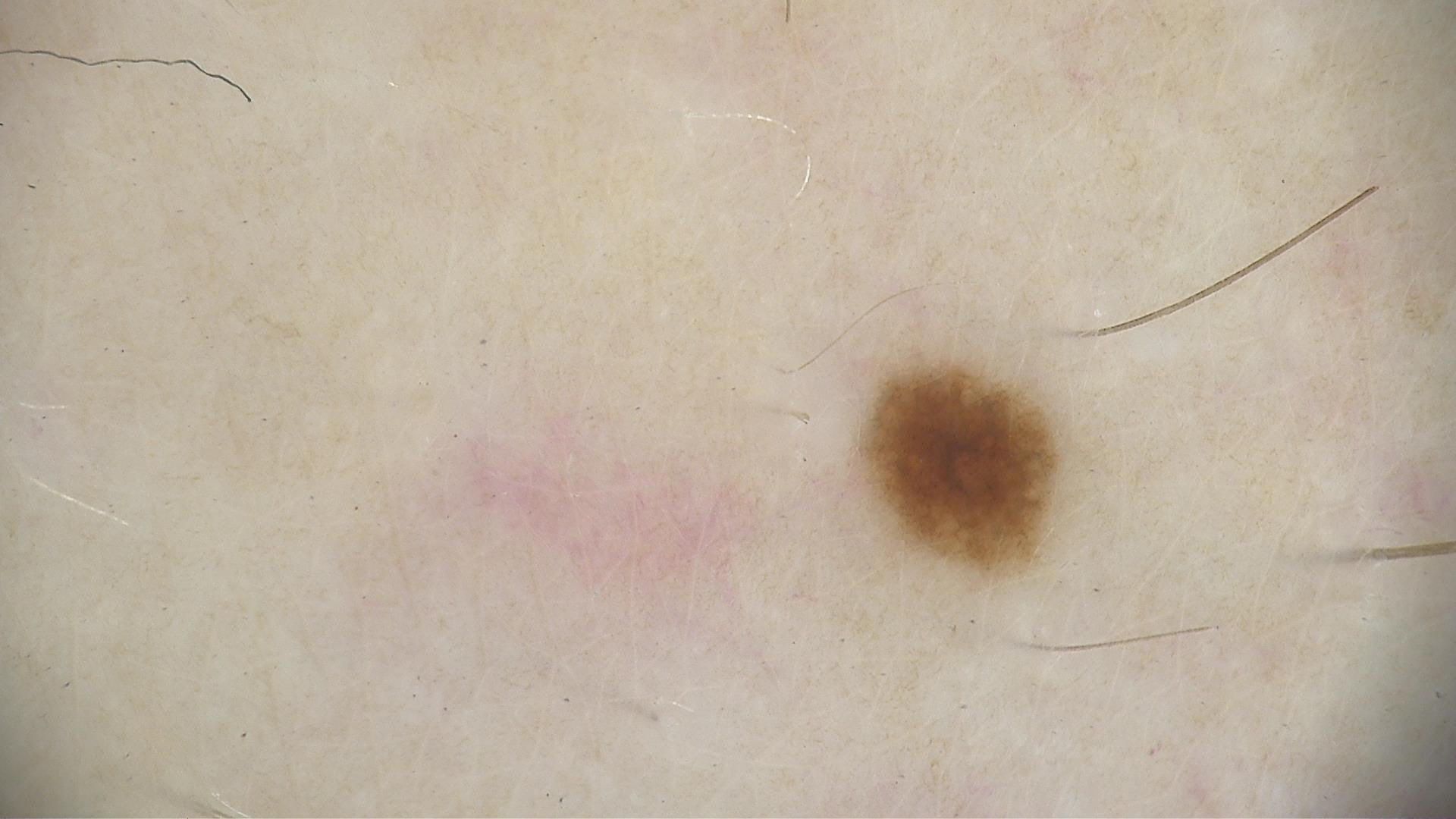  image: dermatoscopy
  diagnosis:
    name: dysplastic junctional nevus
    code: jd
    malignancy: benign
    super_class: melanocytic
    confirmation: expert consensus